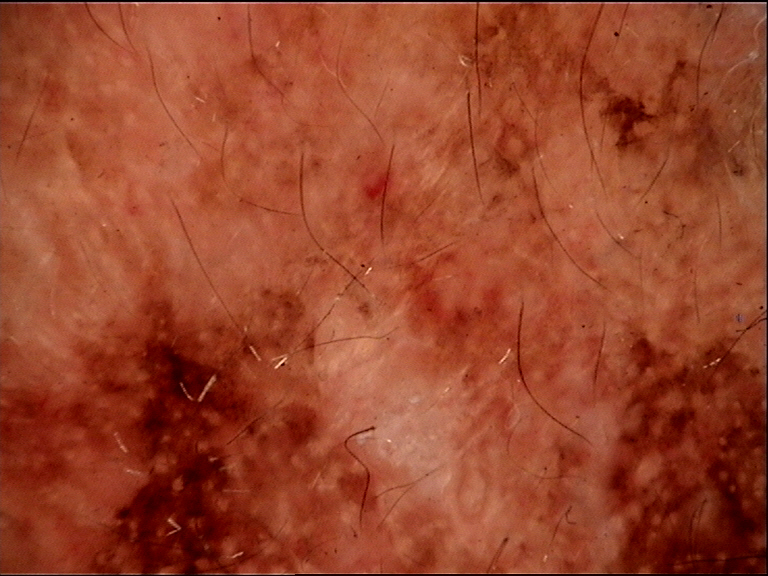Consistent with a keratinocytic lesion — a seborrheic keratosis.